The patient is Fitzpatrick phototype II; a skin lesion imaged with contact-polarized dermoscopy; the chart records a previous melanoma; a male patient roughly 45 years of age — 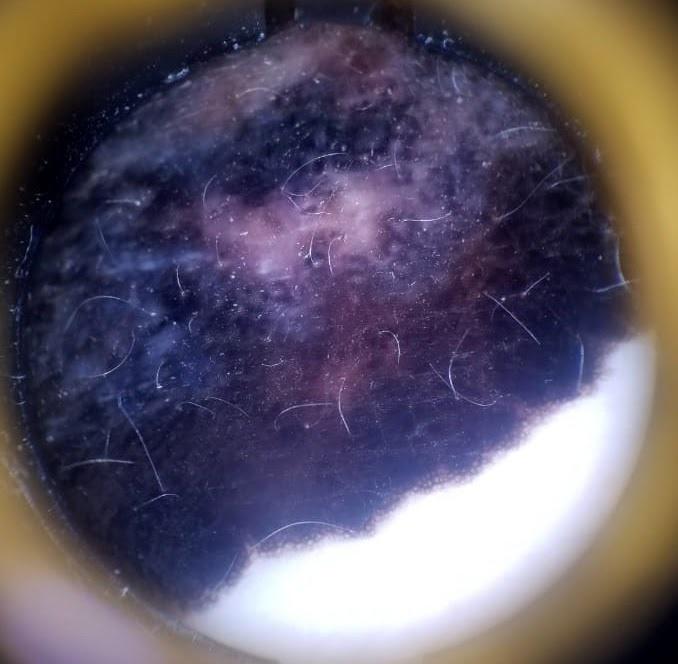| field | value |
|---|---|
| location | the trunk |
| pathology | Melanoma (biopsy-proven) |